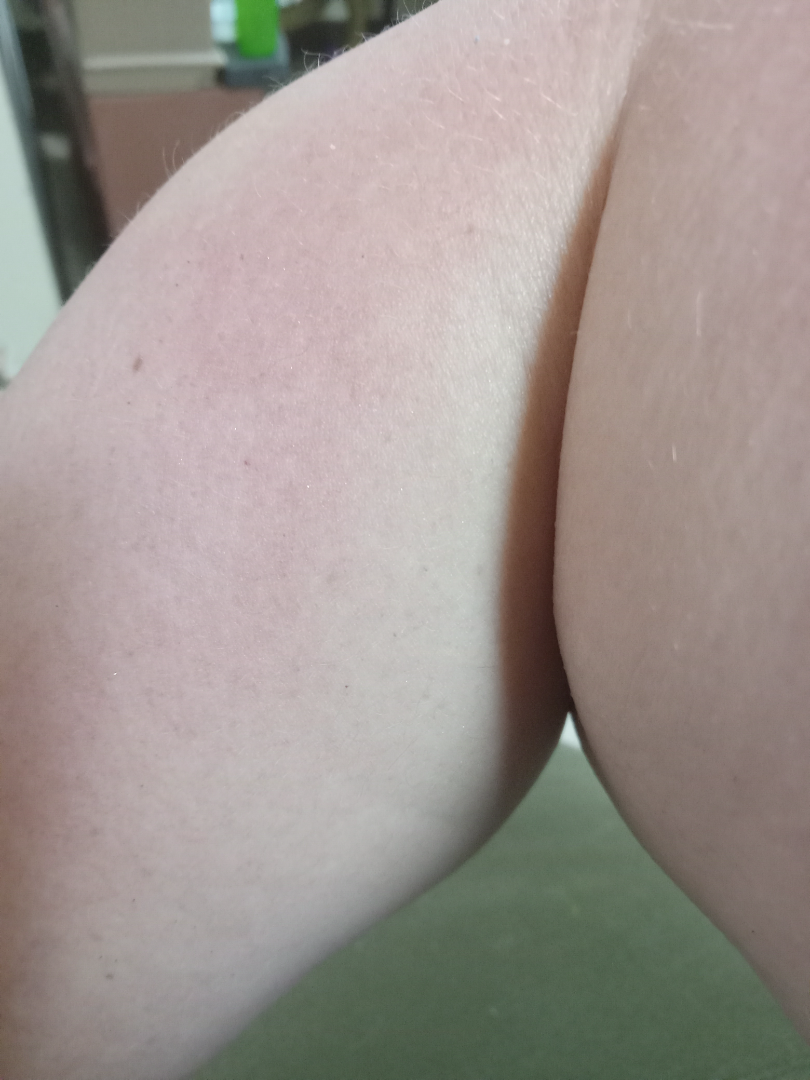| feature | finding |
|---|---|
| assessment | no skin condition identified |